Fitzpatrick IV; lay reviewers estimated 4 on the Monk Skin Tone, the photo was captured at an angle, the lesion involves the head or neck and arm, the condition has been present for one to four weeks, texture is reported as raised or bumpy:
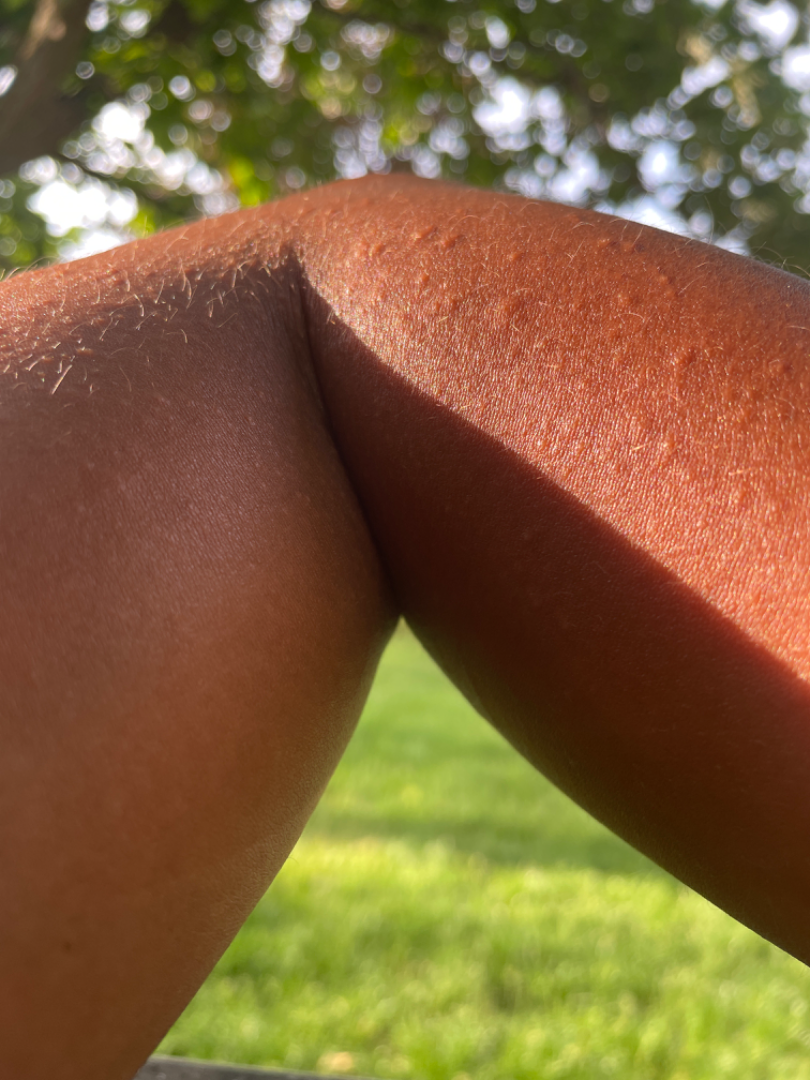Q: What conditions are considered?
A: single-reviewer assessment: most consistent with Eczema; also raised was Lichen nitidus; also consider Allergic Contact Dermatitis